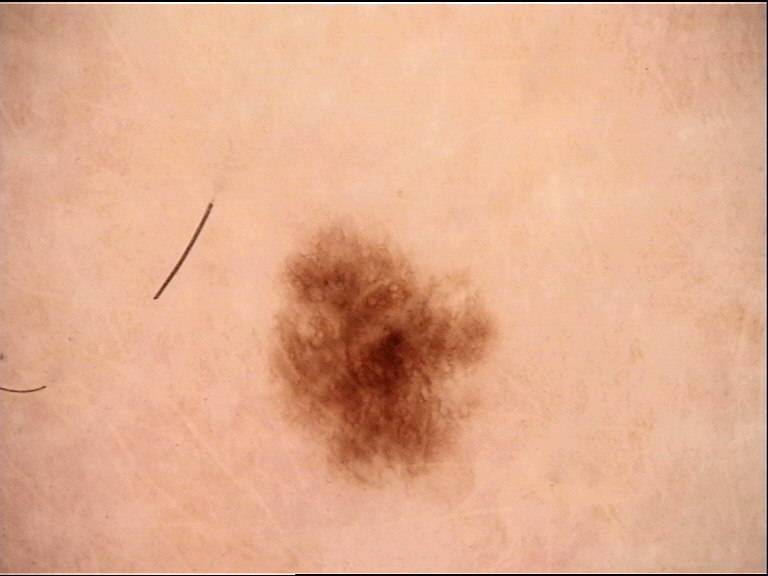Findings: A dermatoscopic image of a skin lesion. Impression: Labeled as a banal lesion — a junctional nevus.